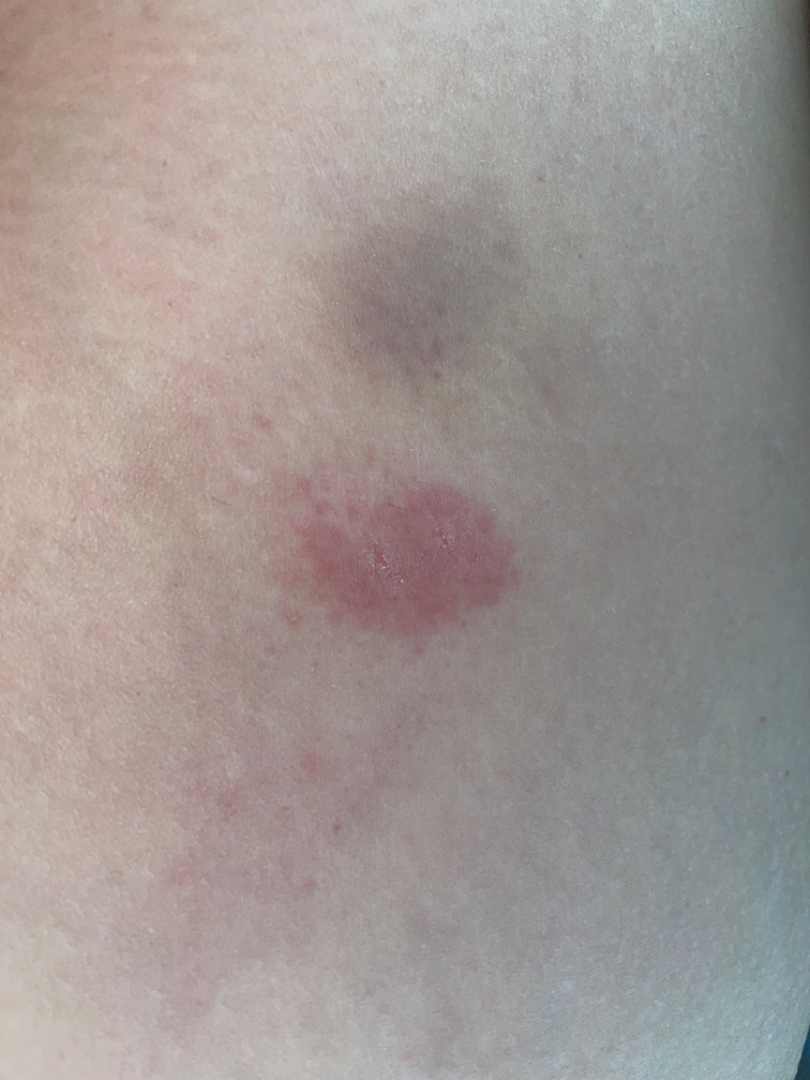The skin findings could not be characterized from the image. The patient reports the lesion is raised or bumpy. A close-up photograph. The lesion is associated with itching and bothersome appearance. The leg is involved. Present for less than one week. No relevant systemic symptoms.